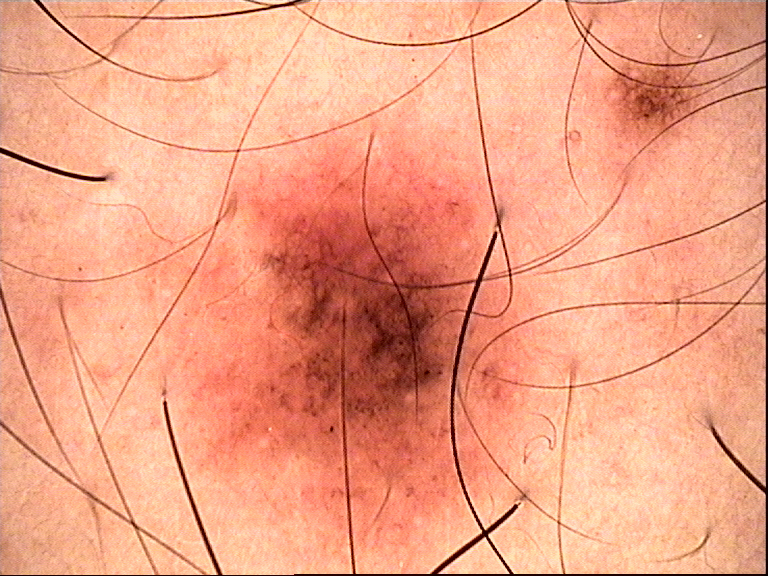| feature | finding |
|---|---|
| modality | dermoscopy |
| label | dysplastic compound nevus (expert consensus) |